A dermoscopic view of a skin lesion — 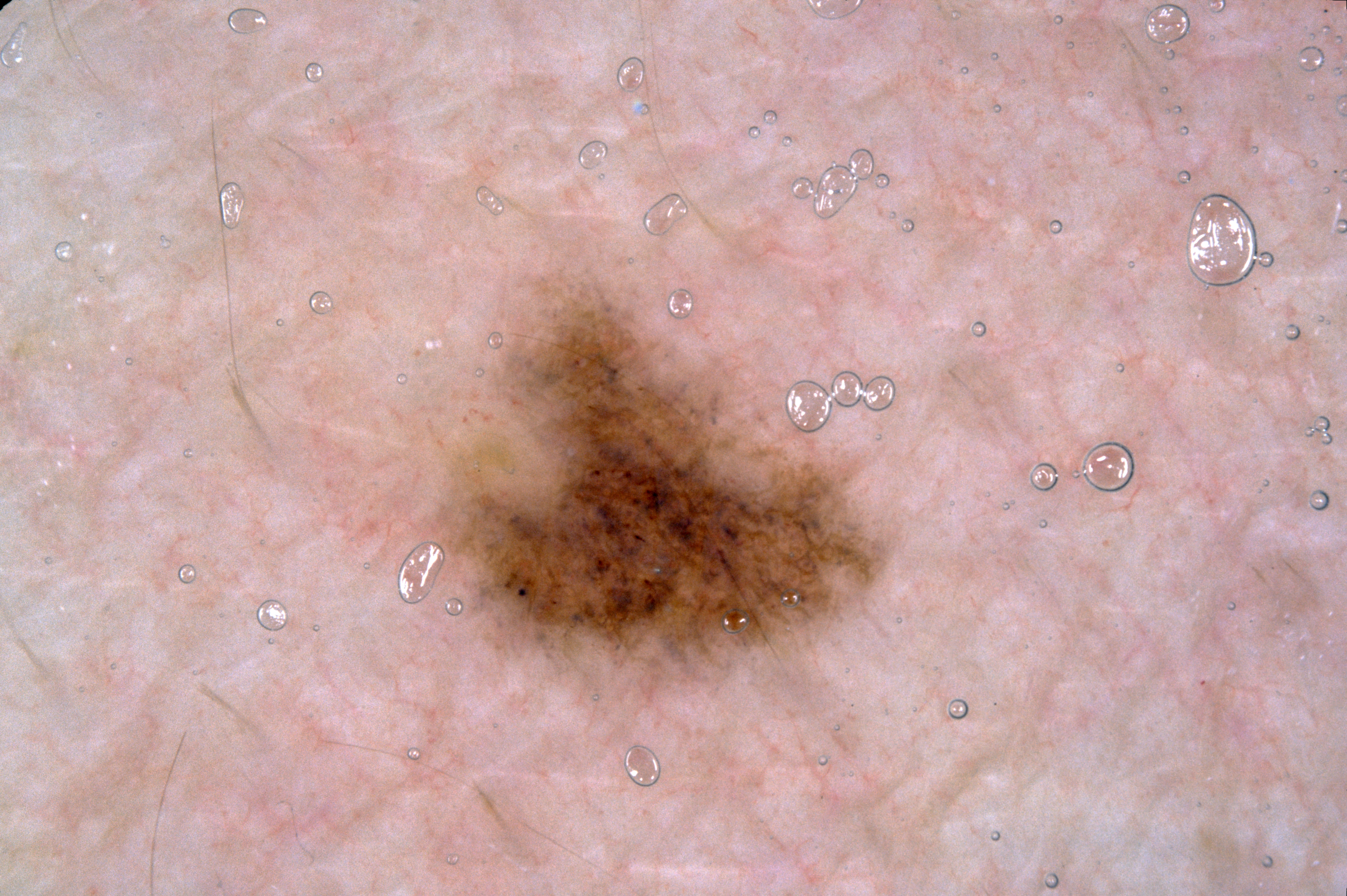Findings: As (left, top, right, bottom), the lesion is bounded by 354, 259, 902, 718. Assessment: Clinically diagnosed as a melanocytic nevus.